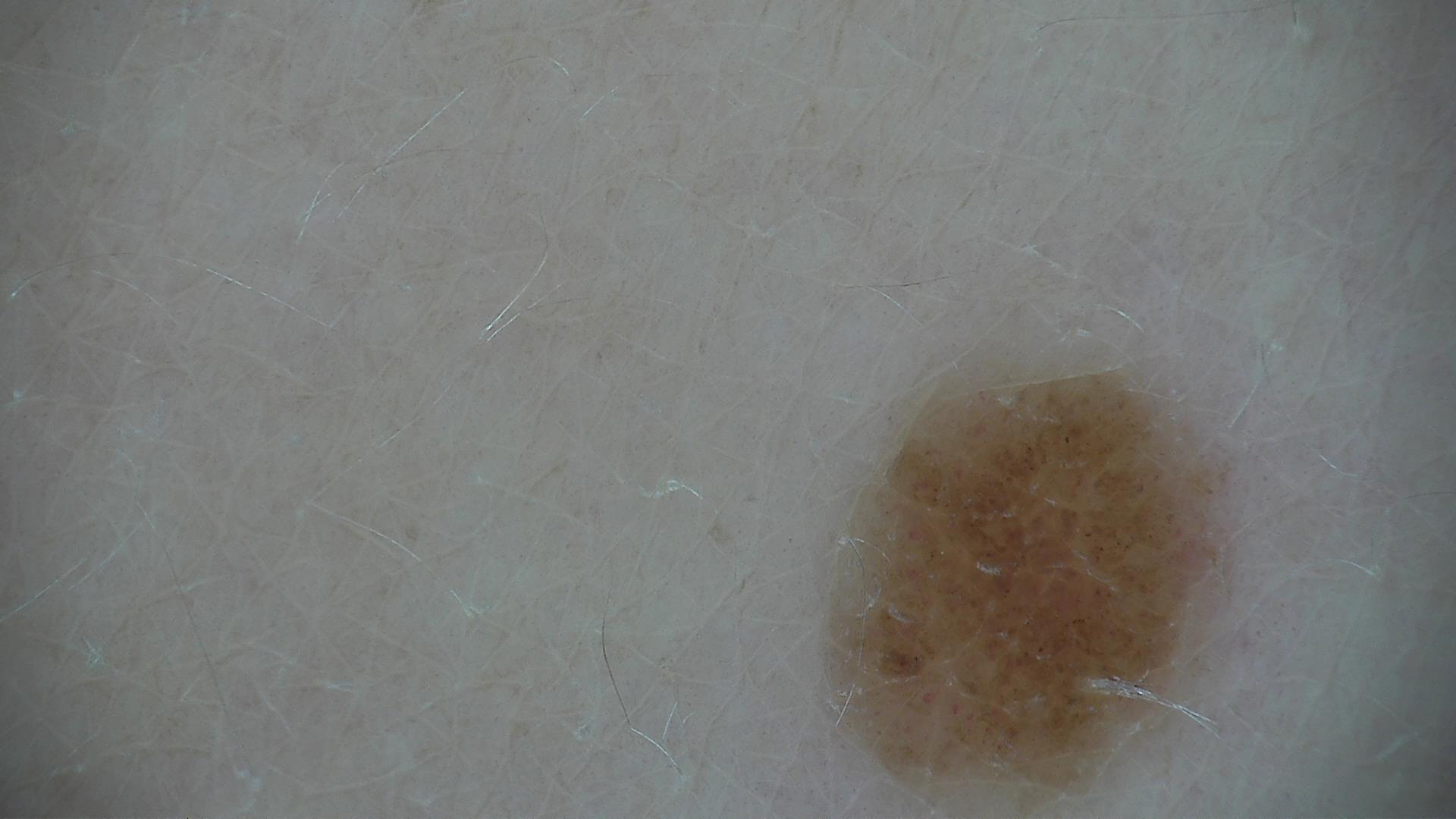Findings:
* class: junctional nevus (expert consensus)